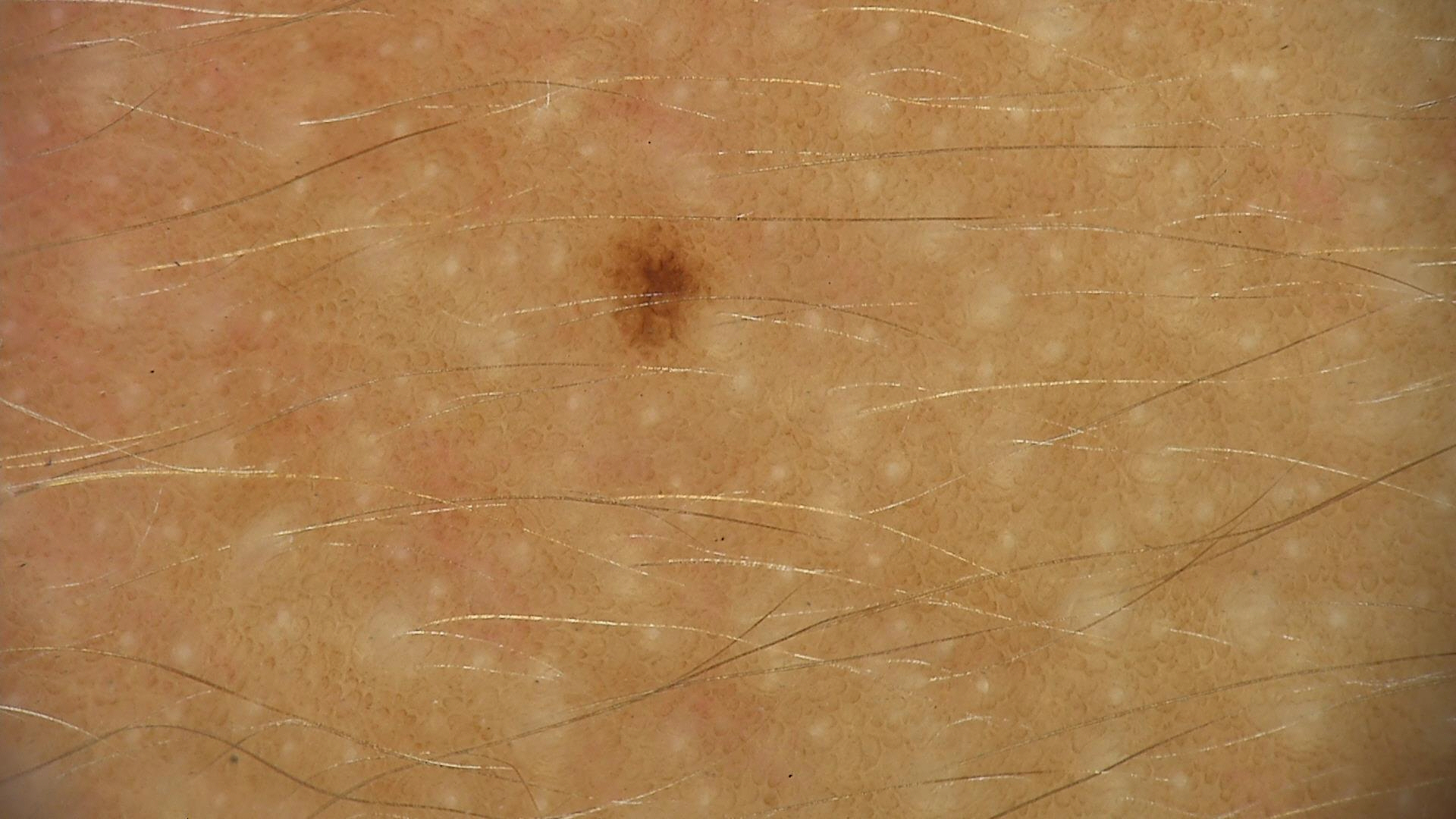assessment: dysplastic junctional nevus (expert consensus)